A dermoscopic image of a skin lesion: 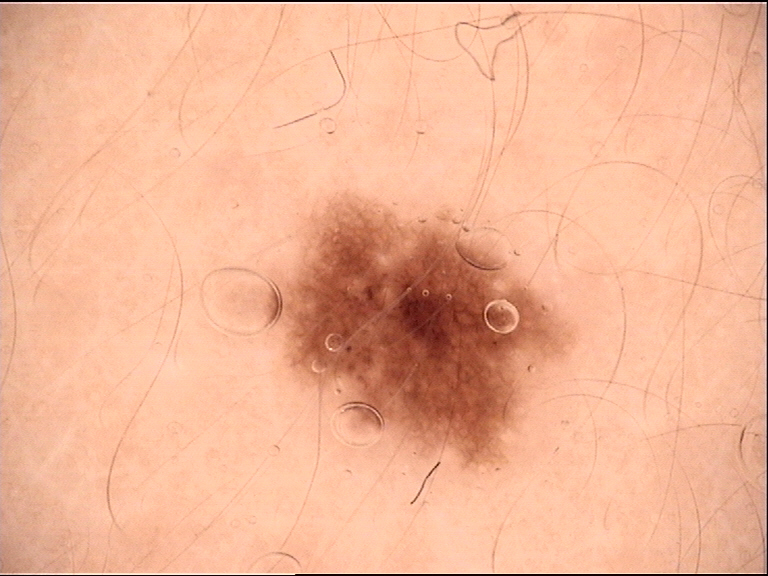The diagnosis was a banal lesion — a junctional nevus.